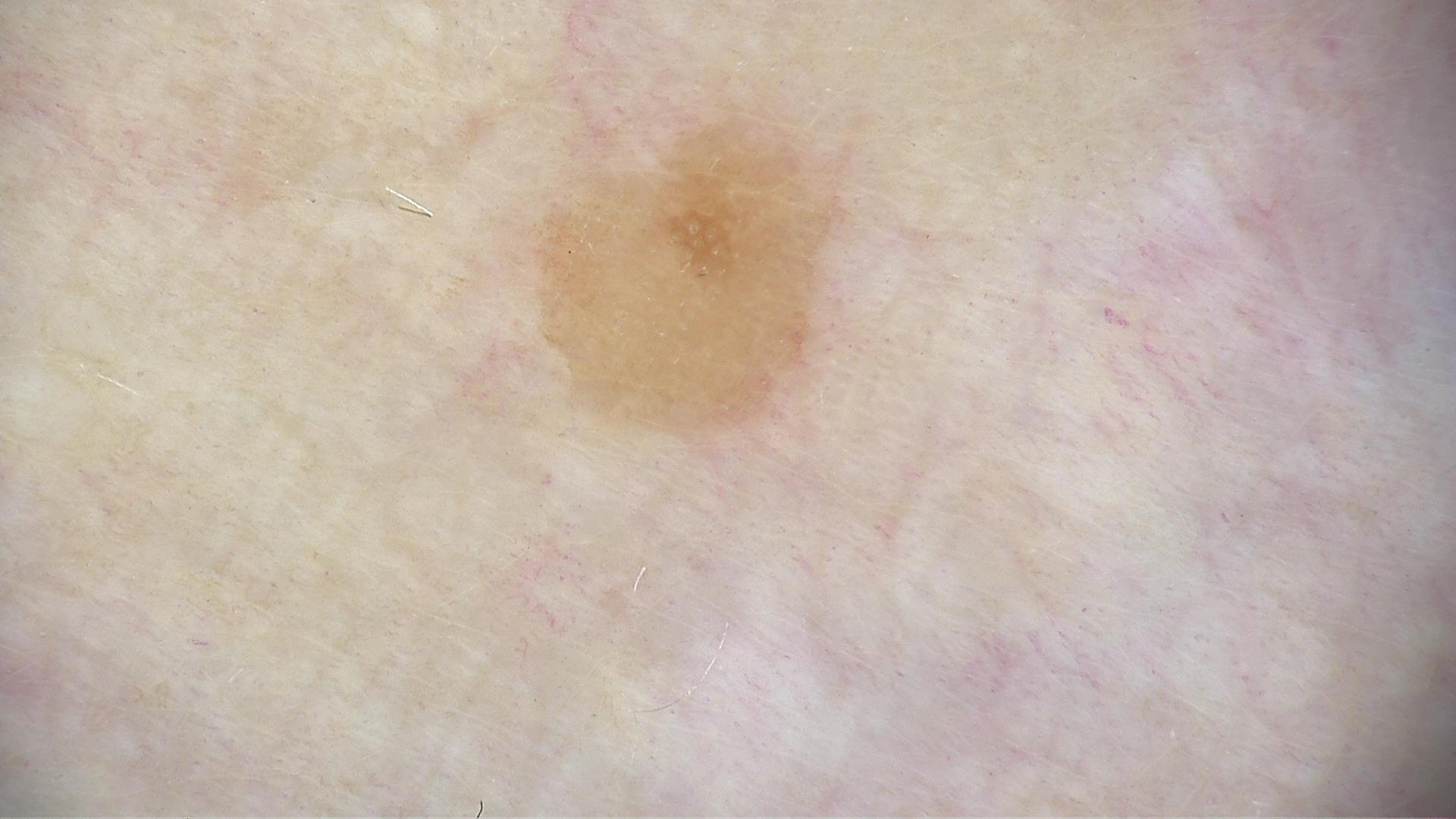modality: dermoscopy, assessment: seborrheic keratosis (expert consensus).